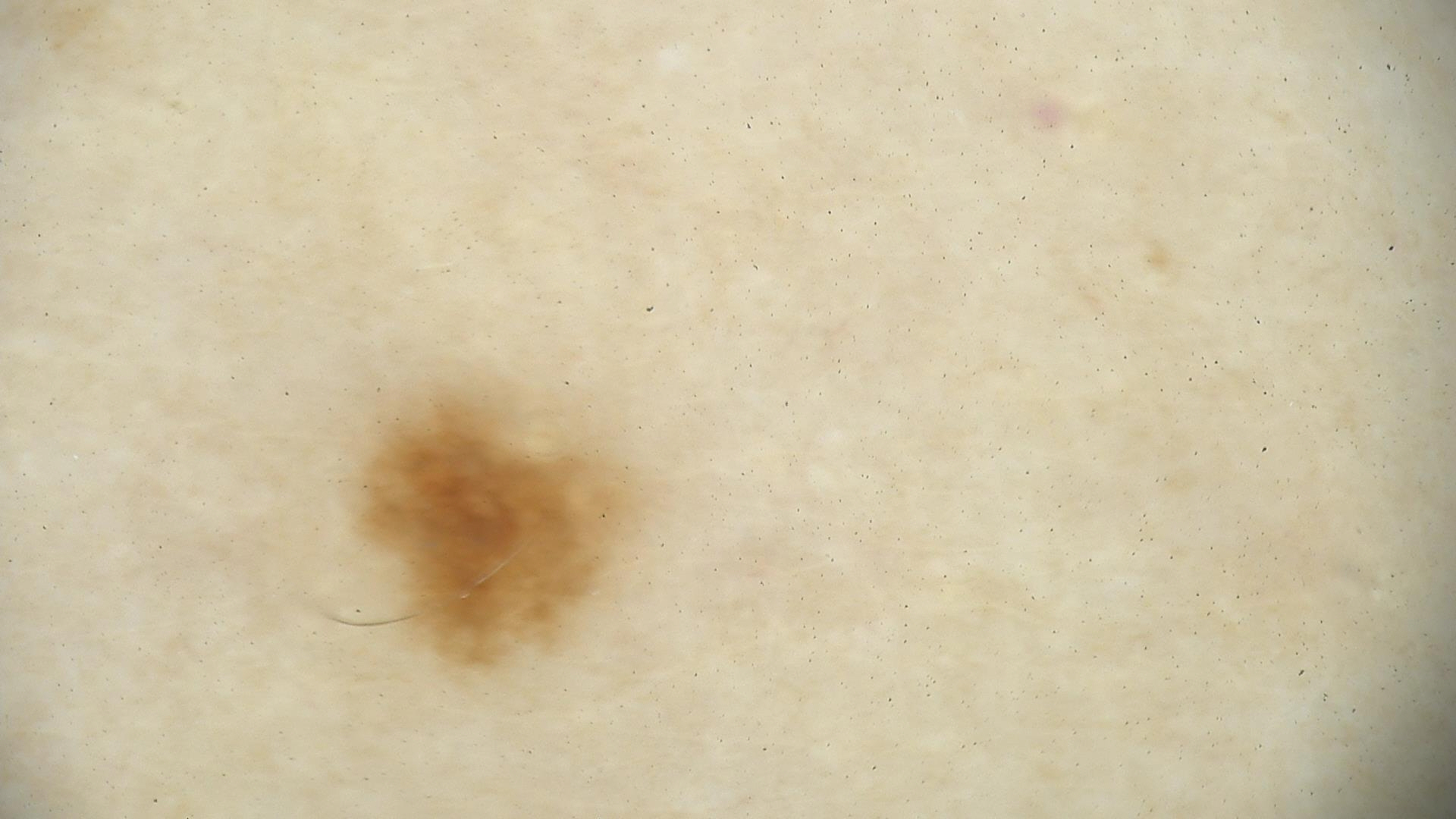diagnosis = dysplastic junctional nevus (expert consensus).